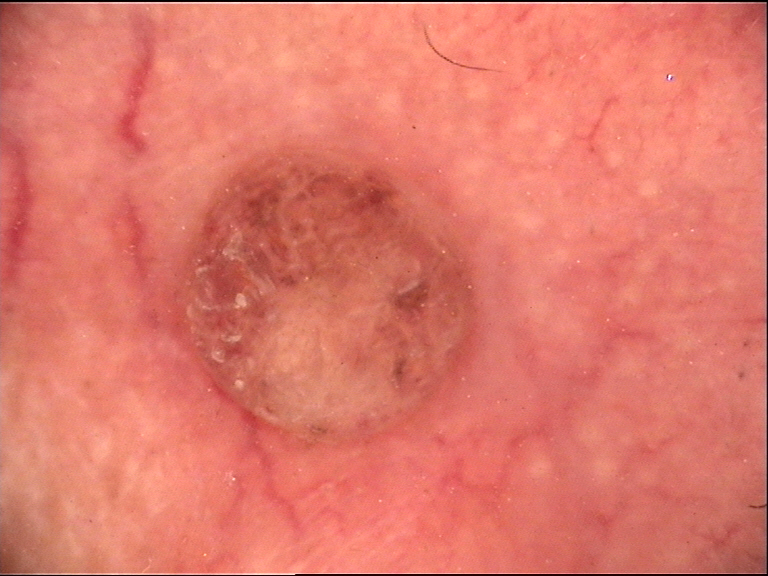Findings:
A dermoscopic close-up of a skin lesion. The morphology is that of a banal lesion.
Impression:
The diagnosis was a dermal nevus.